The lesion is associated with itching; the patient described the issue as a rash; the patient notes the condition has been present for about one day; the photograph is a close-up of the affected area; the lesion involves the leg.
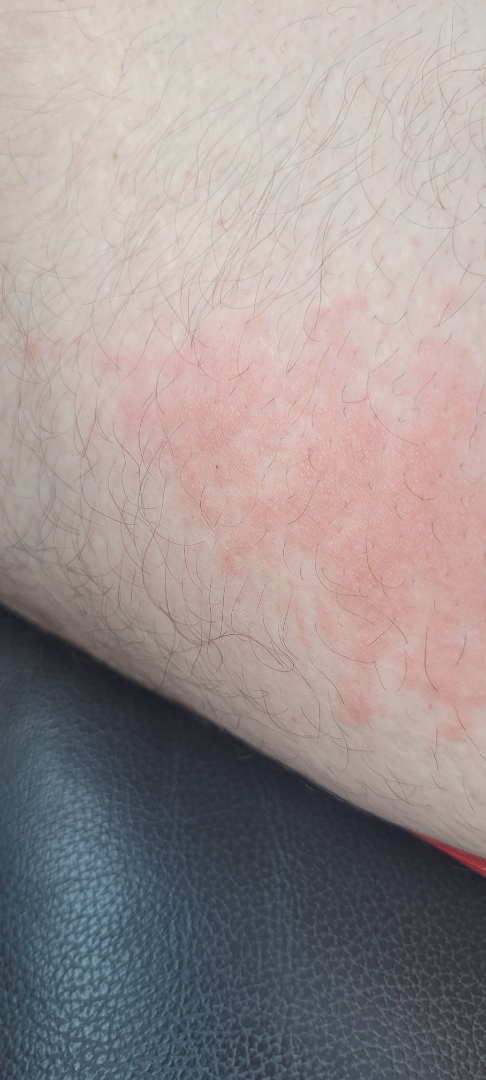The case was indeterminate on photographic review.